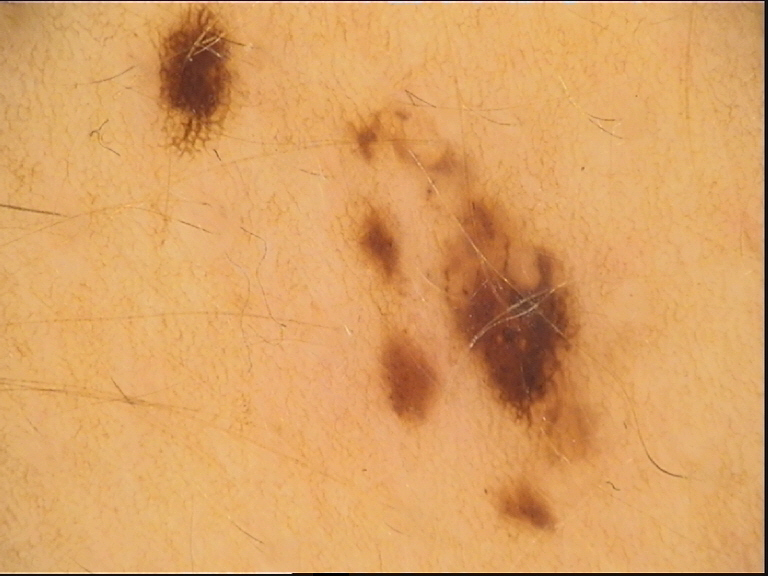• image · dermoscopy
• class · dysplastic junctional nevus (expert consensus)